This image was taken at an angle; the leg is involved — 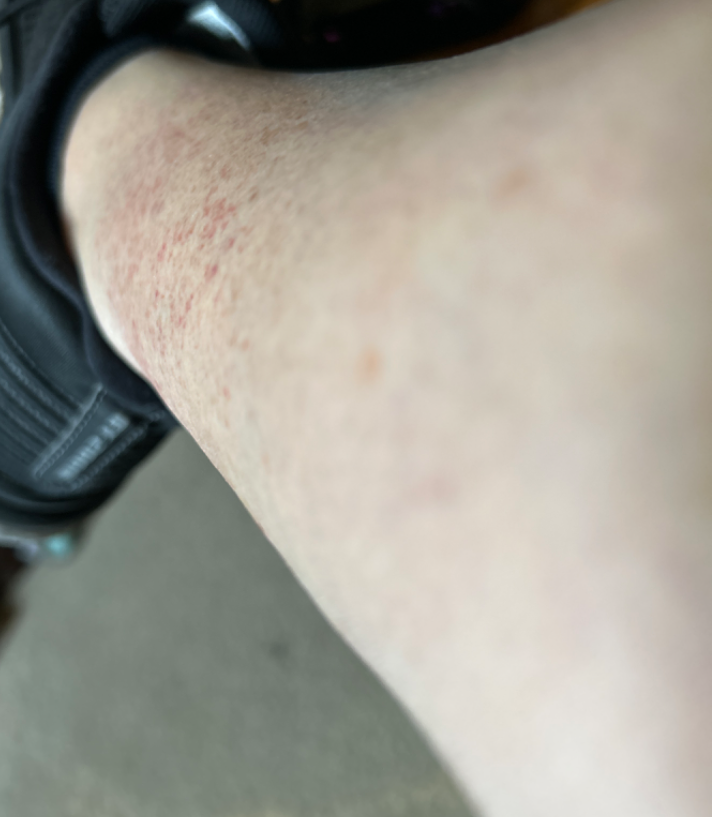constitutional symptoms = fever, joint pain and fatigue | onset = less than one week | differential = a single dermatologist reviewed the case: the leading impression is Leukocytoclastic Vasculitis; with consideration of Pigmented purpuric eruption; also raised was Allergic Contact Dermatitis.